This is a close-up image.
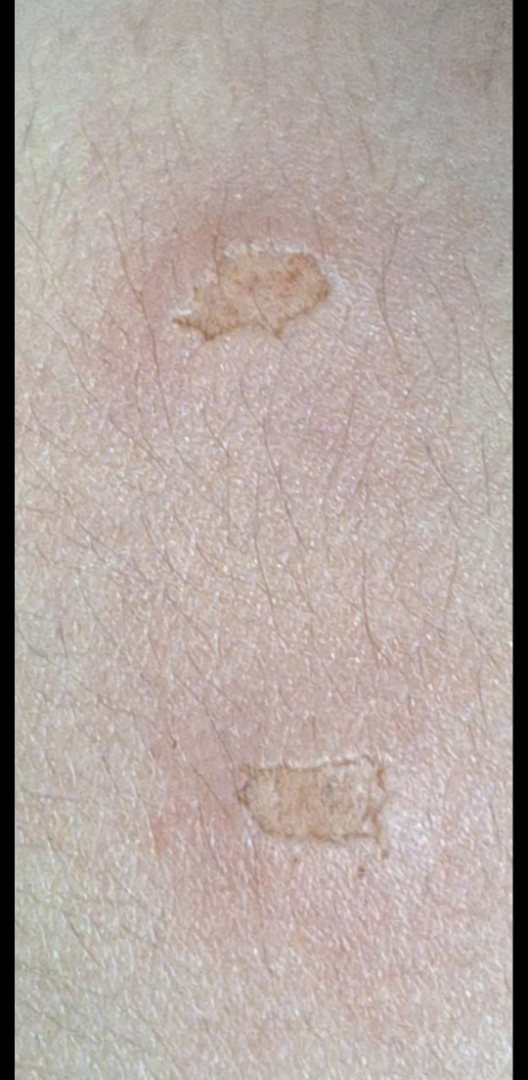The condition could not be reliably identified from the image.